A dermoscopic photograph of a skin lesion: 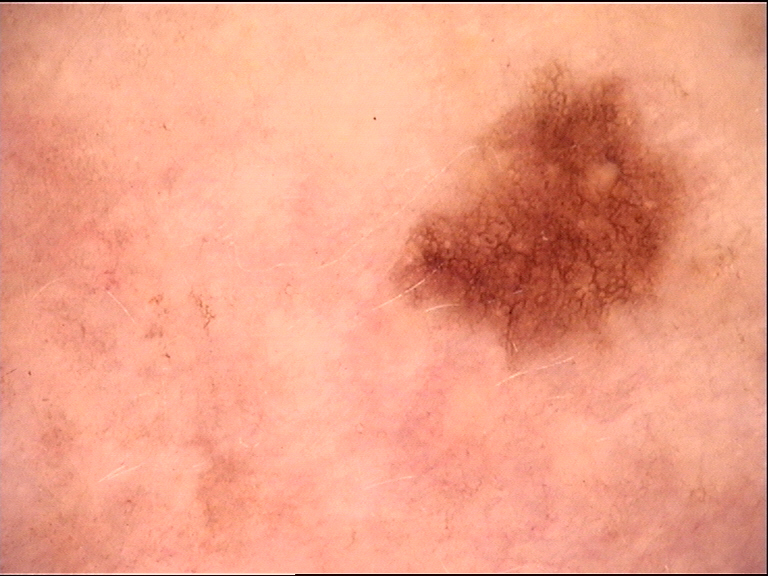  diagnosis:
    name: dysplastic junctional nevus
    code: jd
    malignancy: benign
    super_class: melanocytic
    confirmation: expert consensus